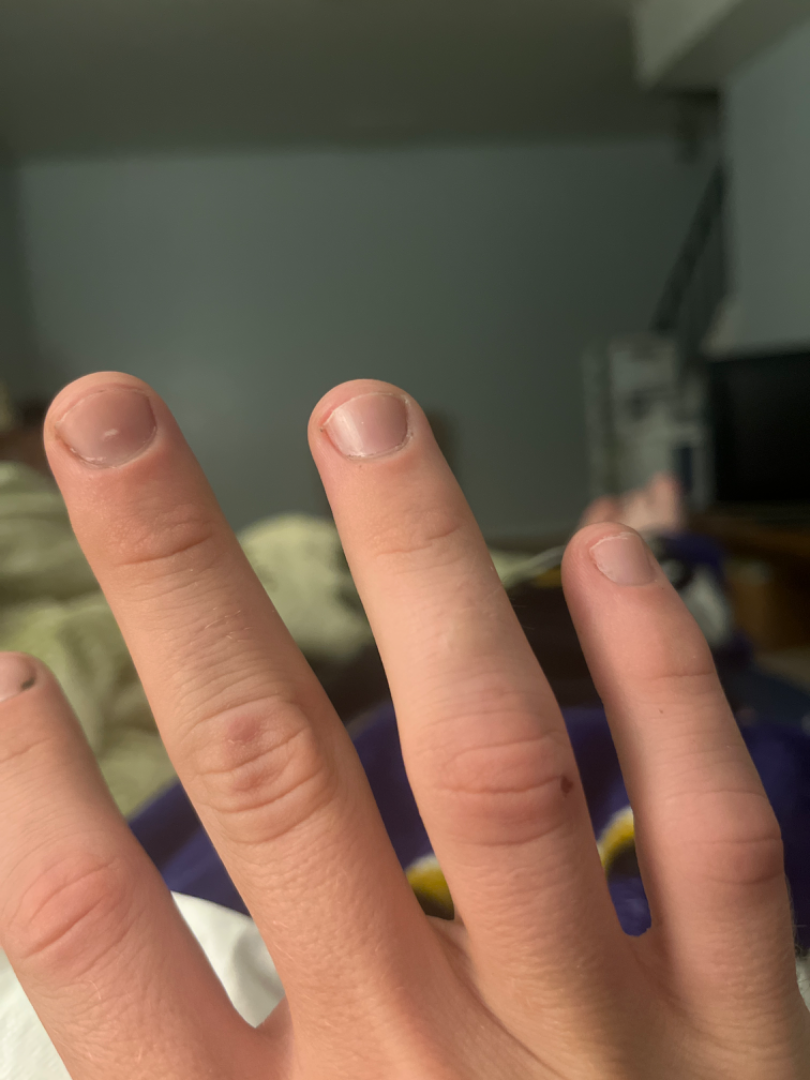- assessment — unable to determine